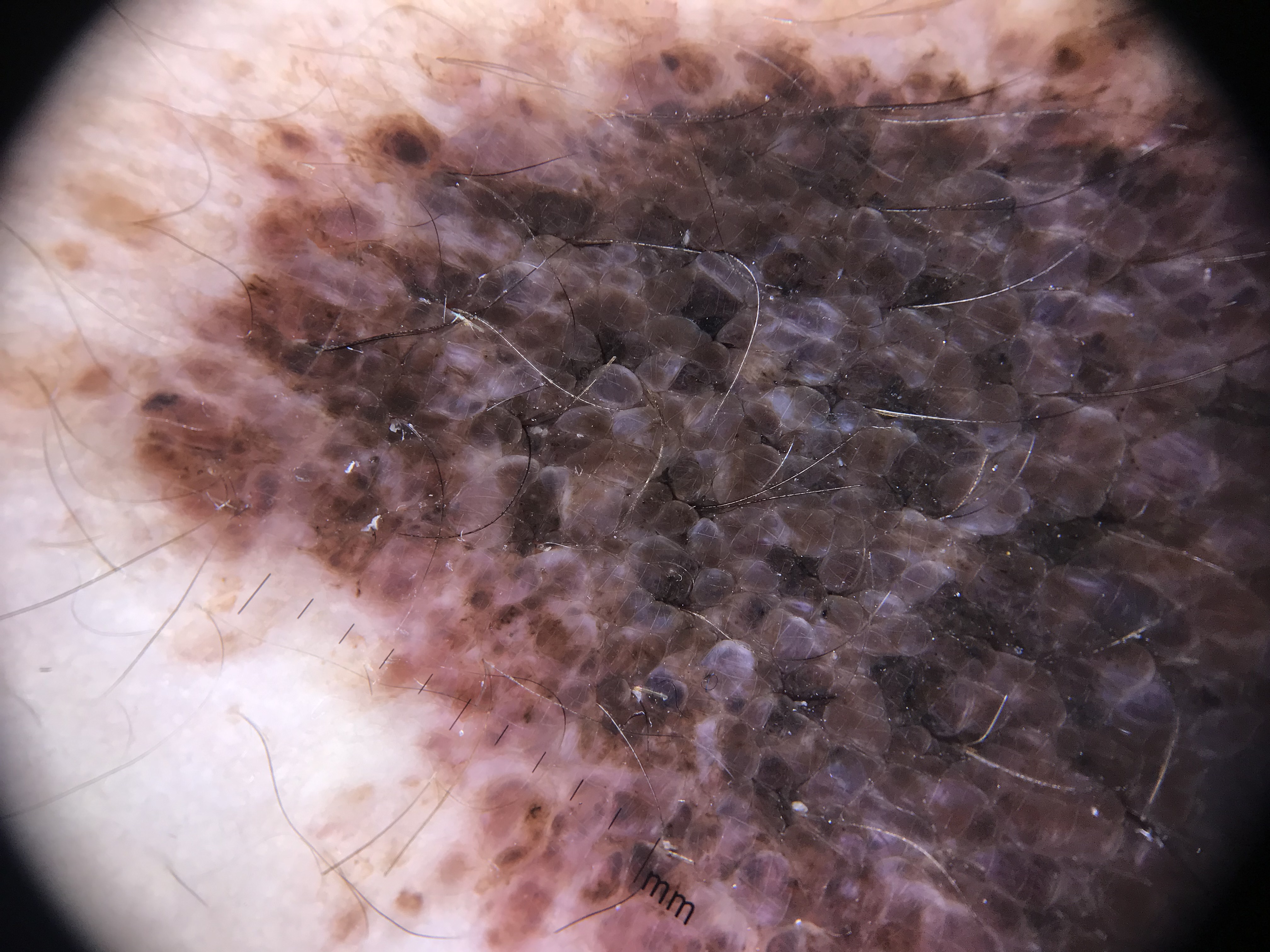This is a banal lesion. Consistent with a congenital compound nevus.